A close-up photograph; the affected area is the arm, back of the hand and leg:
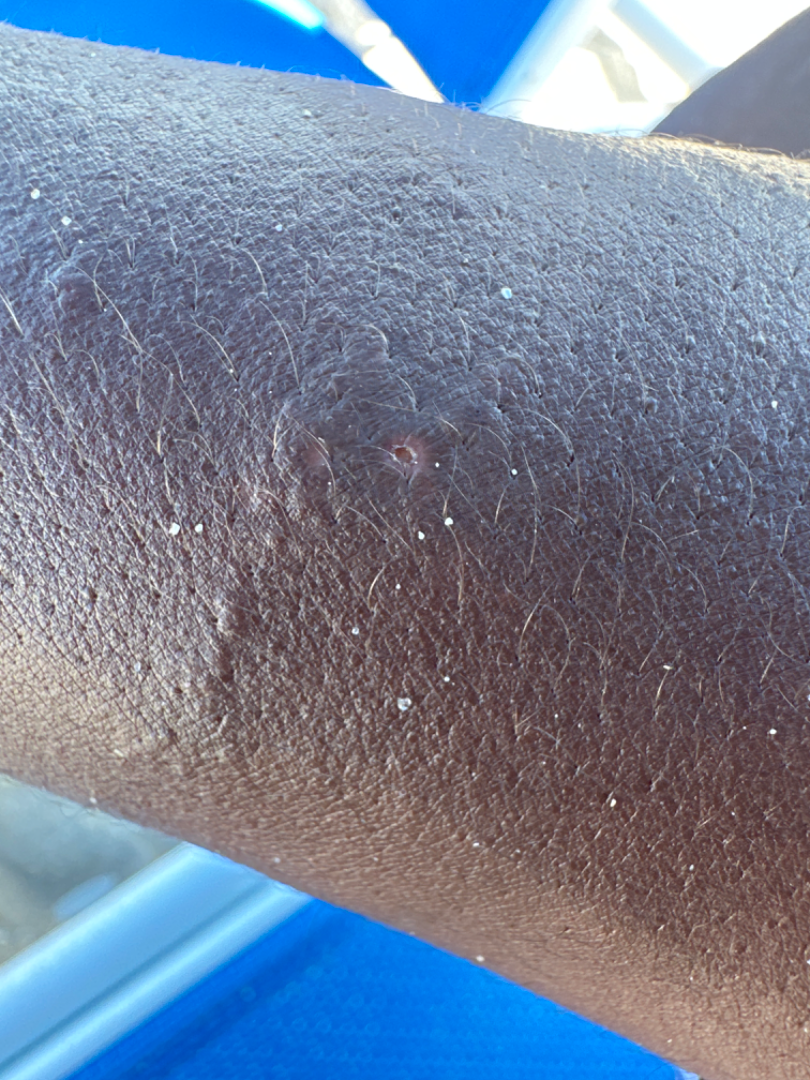The dermatologist could not determine a likely condition from the photograph alone.